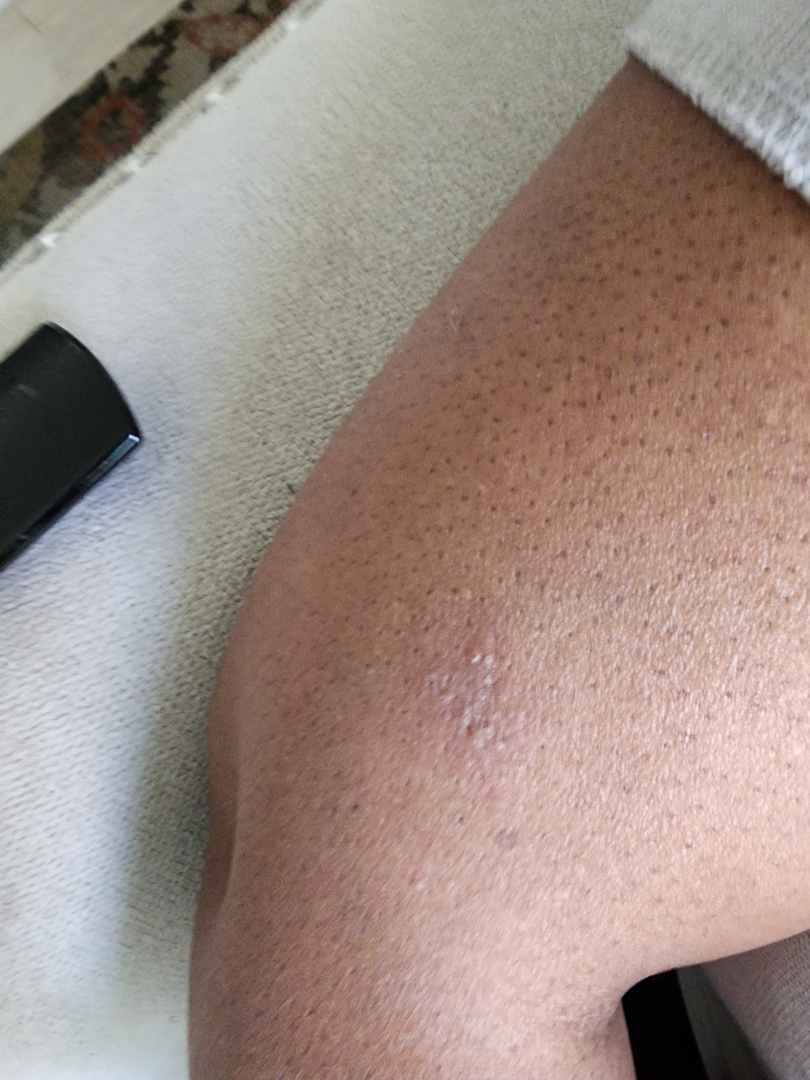Diagnostic features were not clearly distinguishable in this photograph. This is a close-up image. The patient indicates the condition has been present for three to twelve months. Self-categorized by the patient as a rash. Symptoms reported: enlargement and itching. Fitzpatrick phototype V. The affected area is the arm and leg.